This is a close-up image — 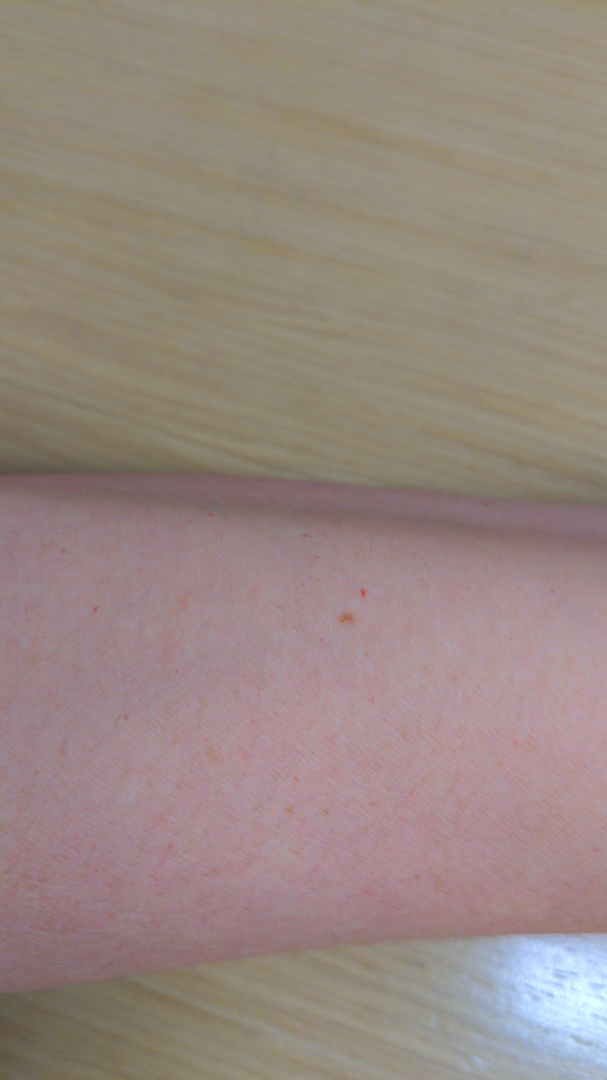Drug Rash (possible); Hypersensitivity (possible).